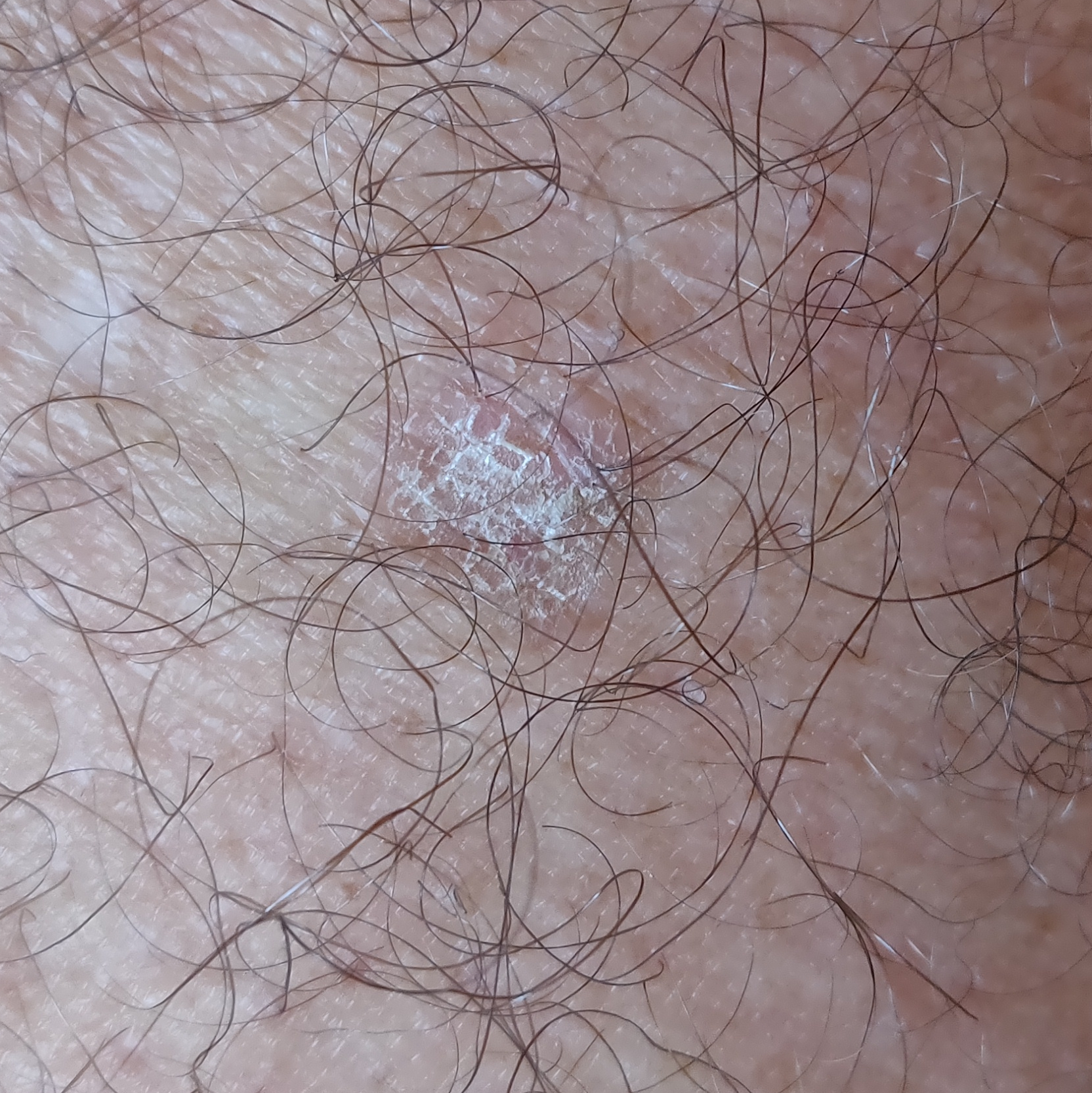A patient 61 years of age.
The patient reports that the lesion itches, is elevated, and has grown.
The consensus clinical diagnosis was a lesion with uncertain malignant potential — an actinic keratosis.